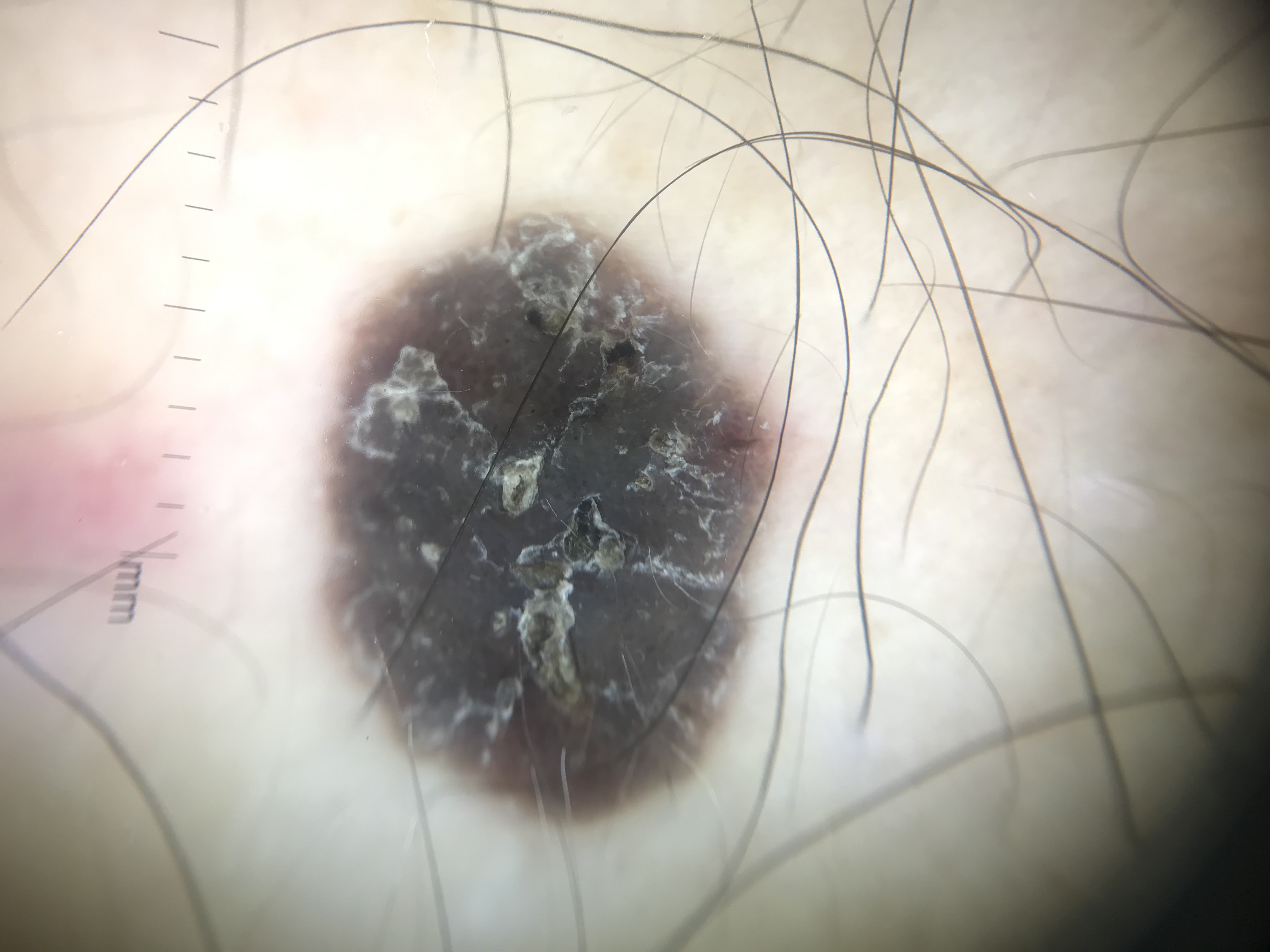Findings:
A dermoscopic image of a skin lesion.
Conclusion:
Consistent with a keratinocytic, benign lesion — a seborrheic keratosis.